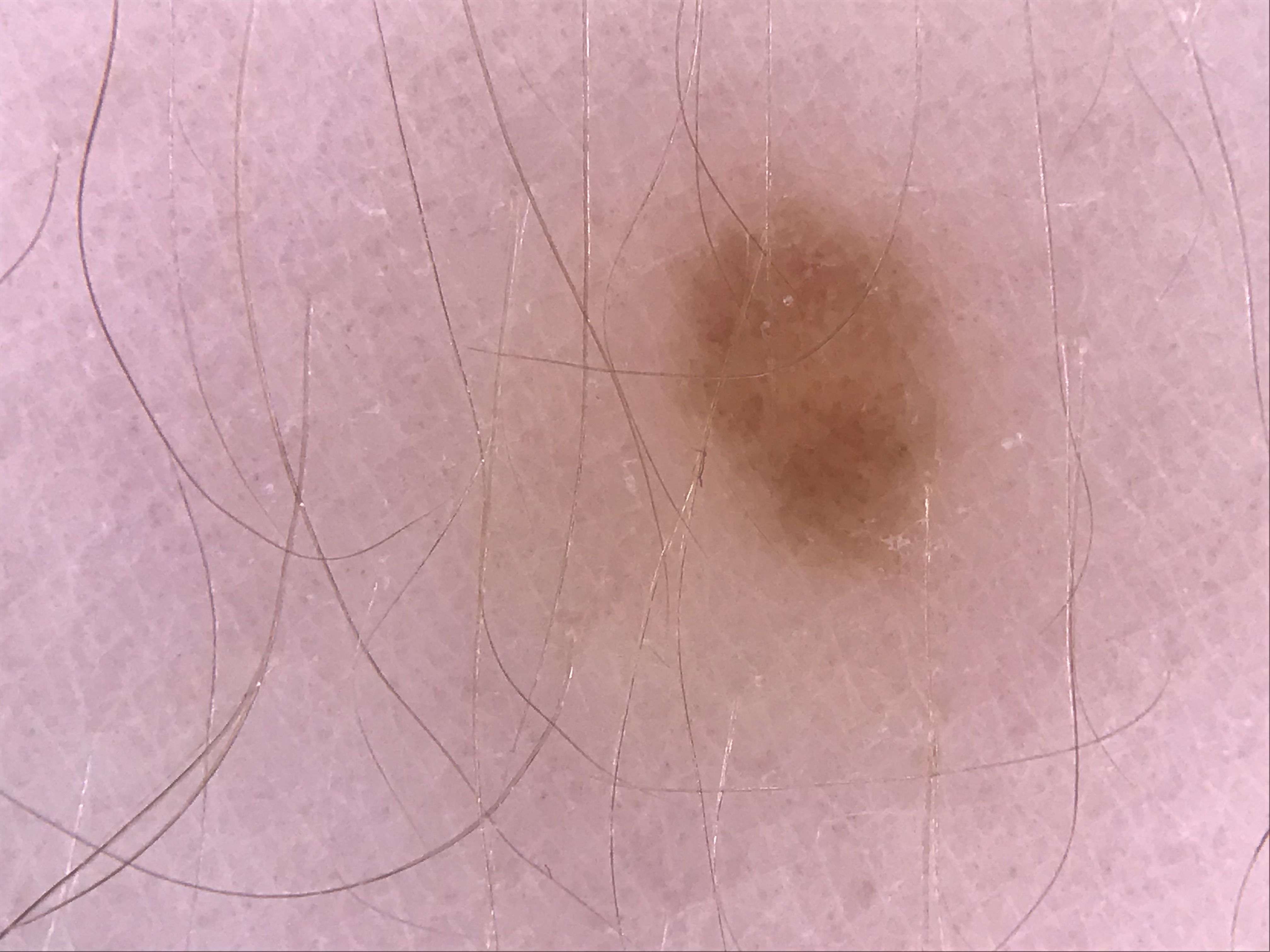A dermatoscopic image of a skin lesion.
Classified as a dysplastic junctional nevus.